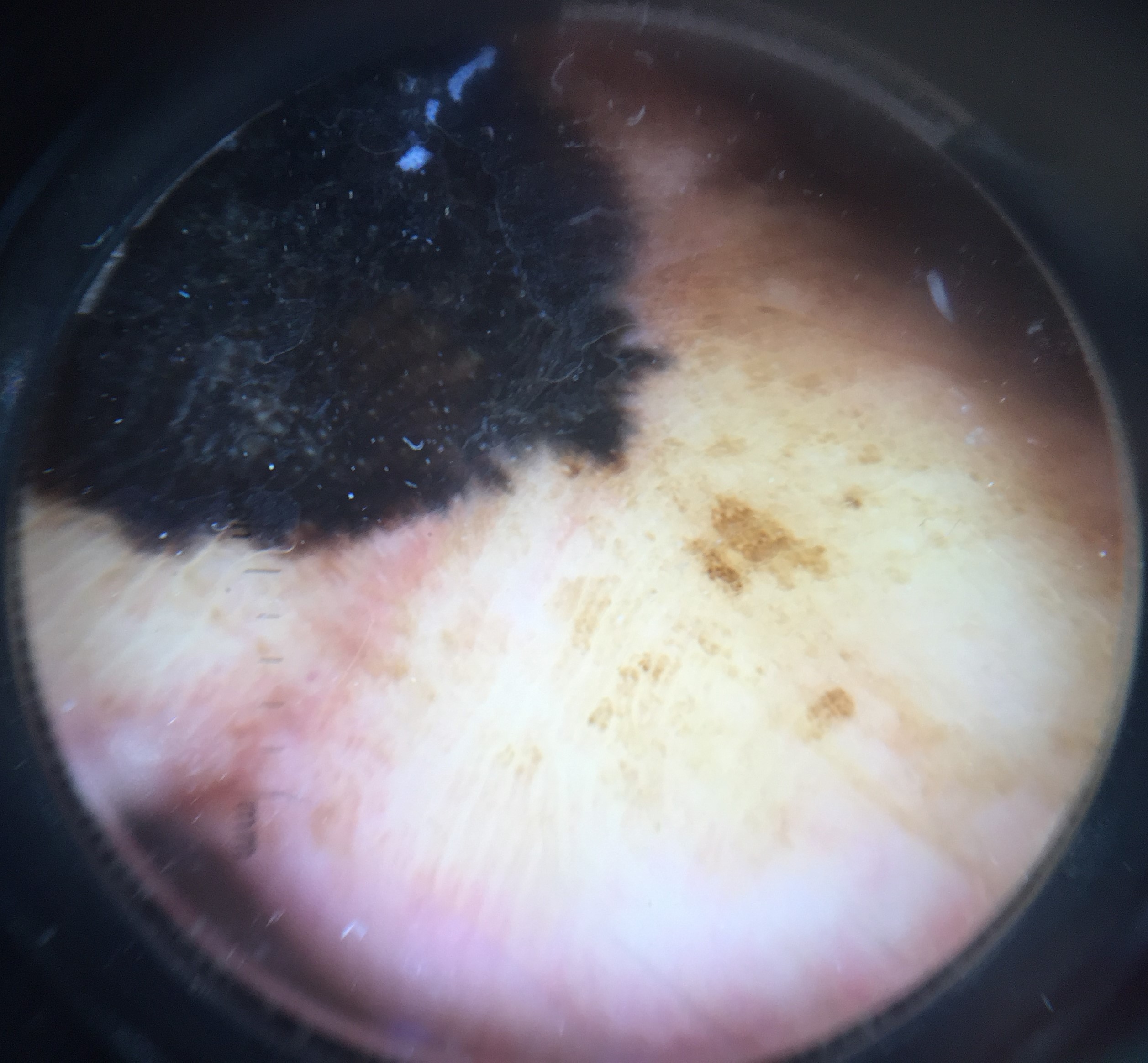image type = dermatoscopy; label = acral lentiginous melanoma (biopsy-proven).